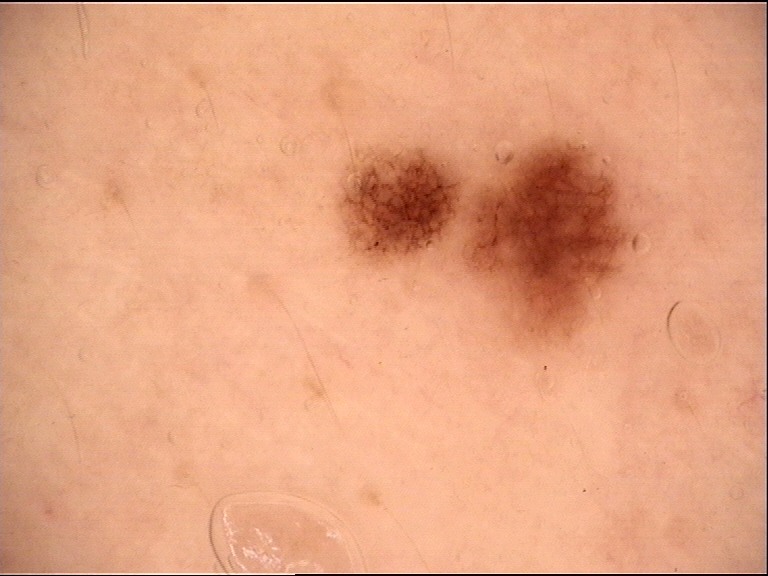A dermoscopy image of a single skin lesion.
The diagnostic label was a benign lesion — a dysplastic junctional nevus.